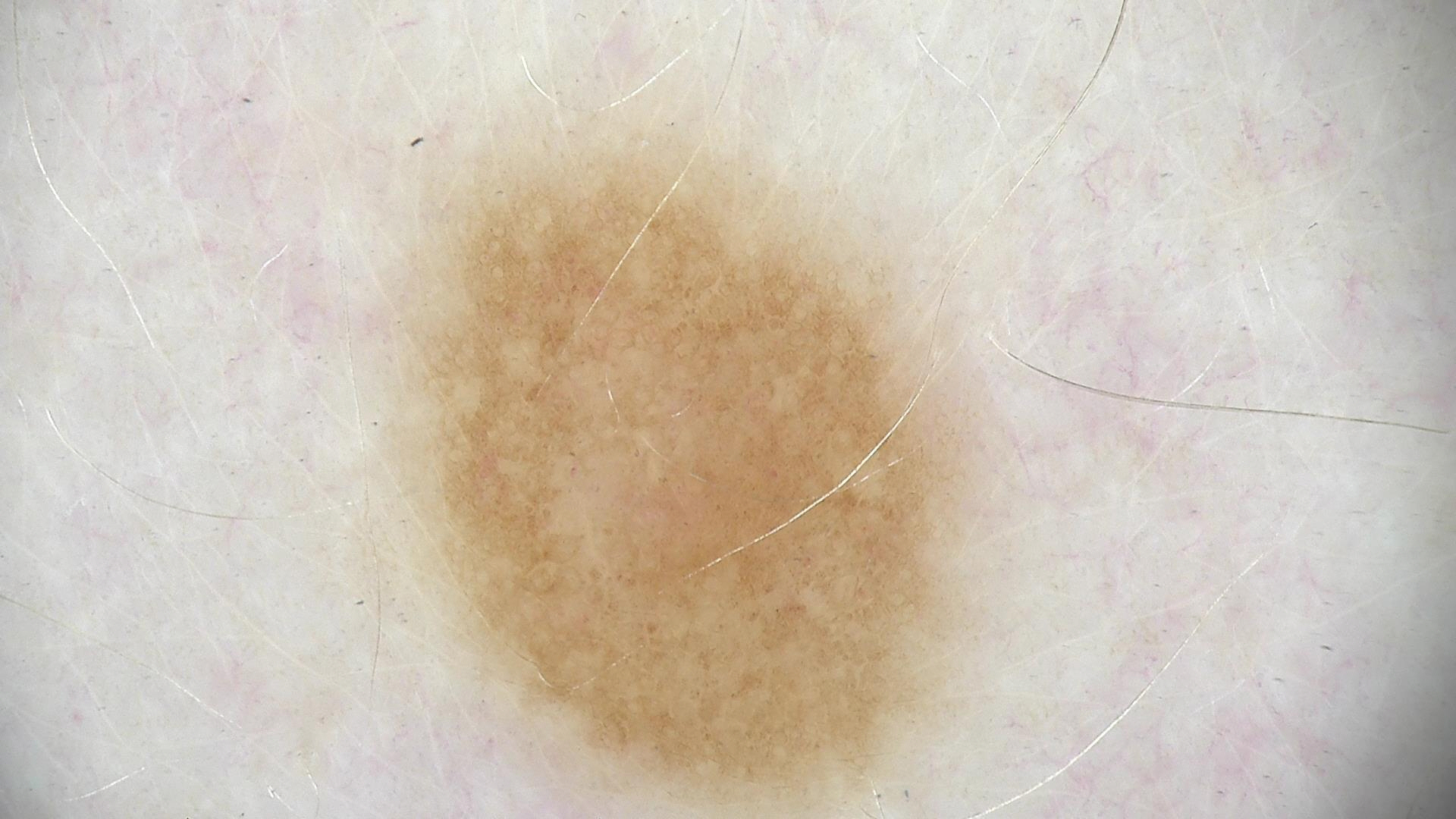modality = dermatoscopy; class = dysplastic junctional nevus (expert consensus).